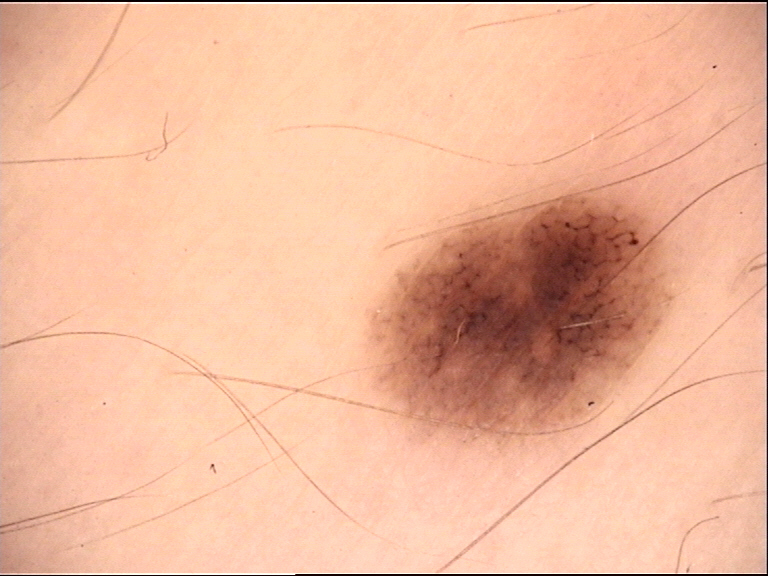– imaging · dermoscopy
– assessment · dysplastic junctional nevus (expert consensus)